A dermoscopic photograph of a skin lesion.
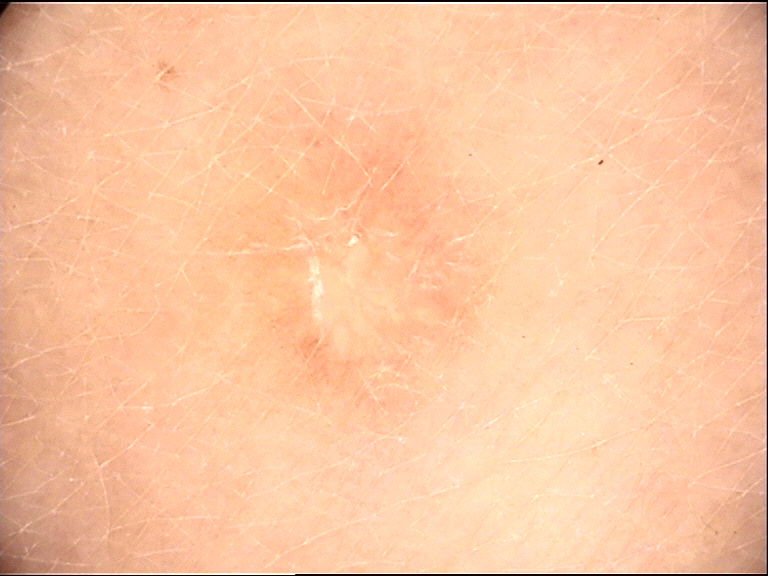lesion type — fibro-histiocytic | class — dermatofibroma (expert consensus).